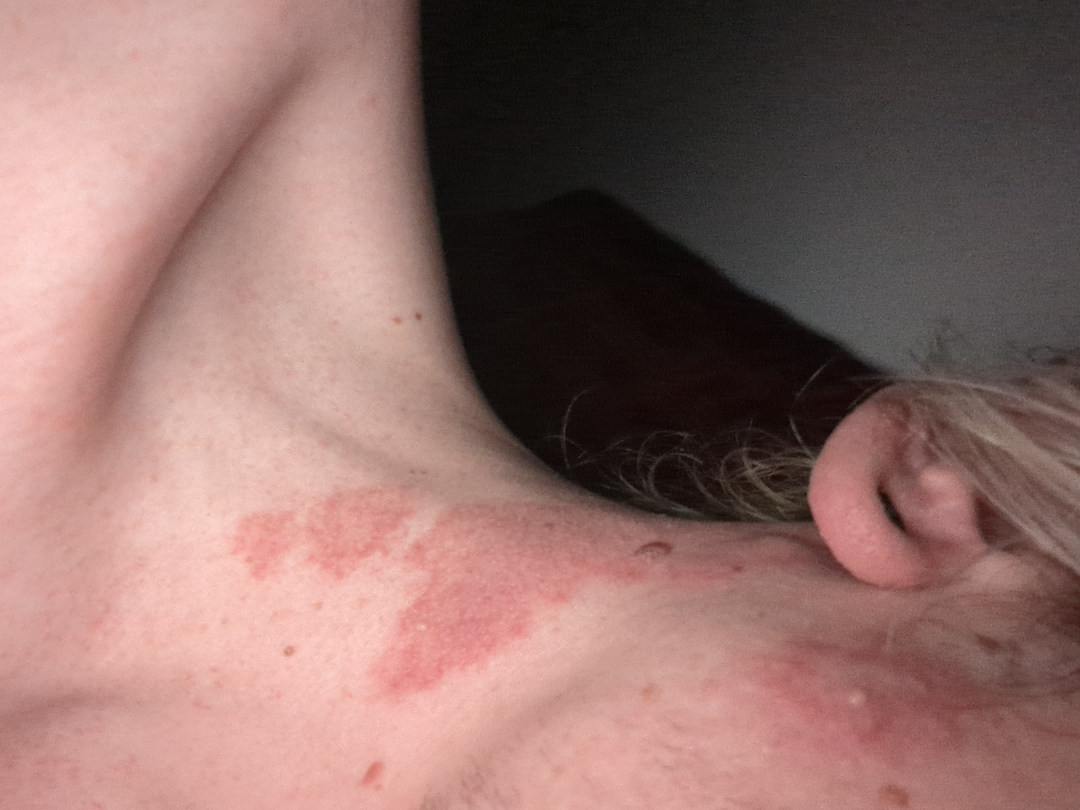Q: What is the lesion texture?
A: flat and raised or bumpy
Q: Reported symptoms?
A: darkening
Q: Anatomic location?
A: head or neck
Q: What is the patient's skin tone?
A: Fitzpatrick I; human graders estimated 2 on the MST
Q: Age and sex?
A: male, age 18–29
Q: What is the framing?
A: at an angle
Q: How does the patient describe it?
A: a pigmentary problem
Q: Constitutional symptoms?
A: none reported
Q: When did this start?
A: since childhood
Q: What conditions are considered?
A: Tinea, Allergic Contact Dermatitis and Cutaneous lupus were each considered, in no particular order